The patient notes bothersome appearance · the lesion is described as rough or flaky · non-clinician graders estimated MST 3–4 · an image taken at a distance · self-categorized by the patient as a rash: 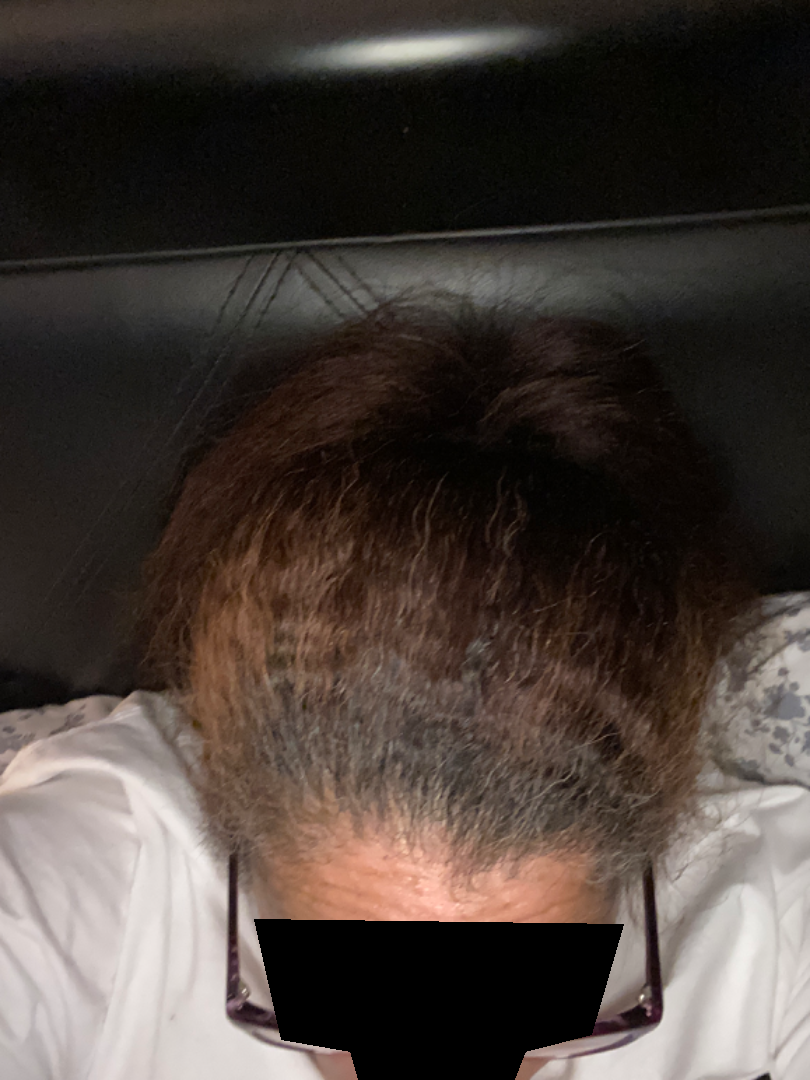Case summary:
– assessment — indeterminate